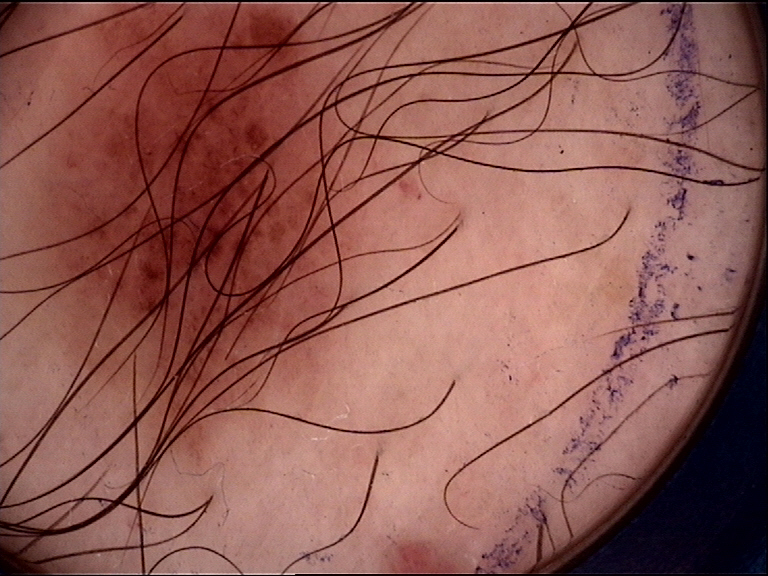A dermoscopic photograph of a skin lesion. Diagnosed as a dysplastic junctional nevus.